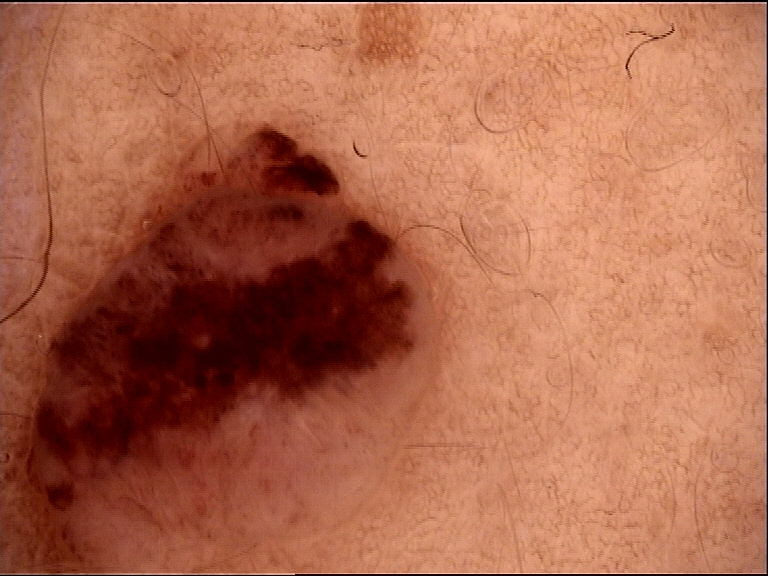Findings:
A skin lesion imaged with a dermatoscope. The morphology is that of a banal lesion.
Impression:
Labeled as a compound nevus.